A dermatoscopic image of a skin lesion.
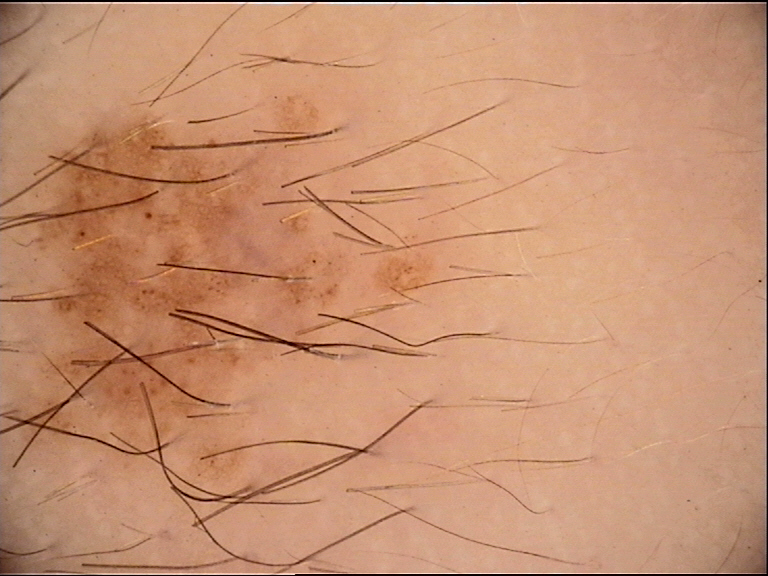The morphology is that of a banal lesion. The diagnostic label was a congenital compound nevus.